A dermoscopic image of a skin lesion.
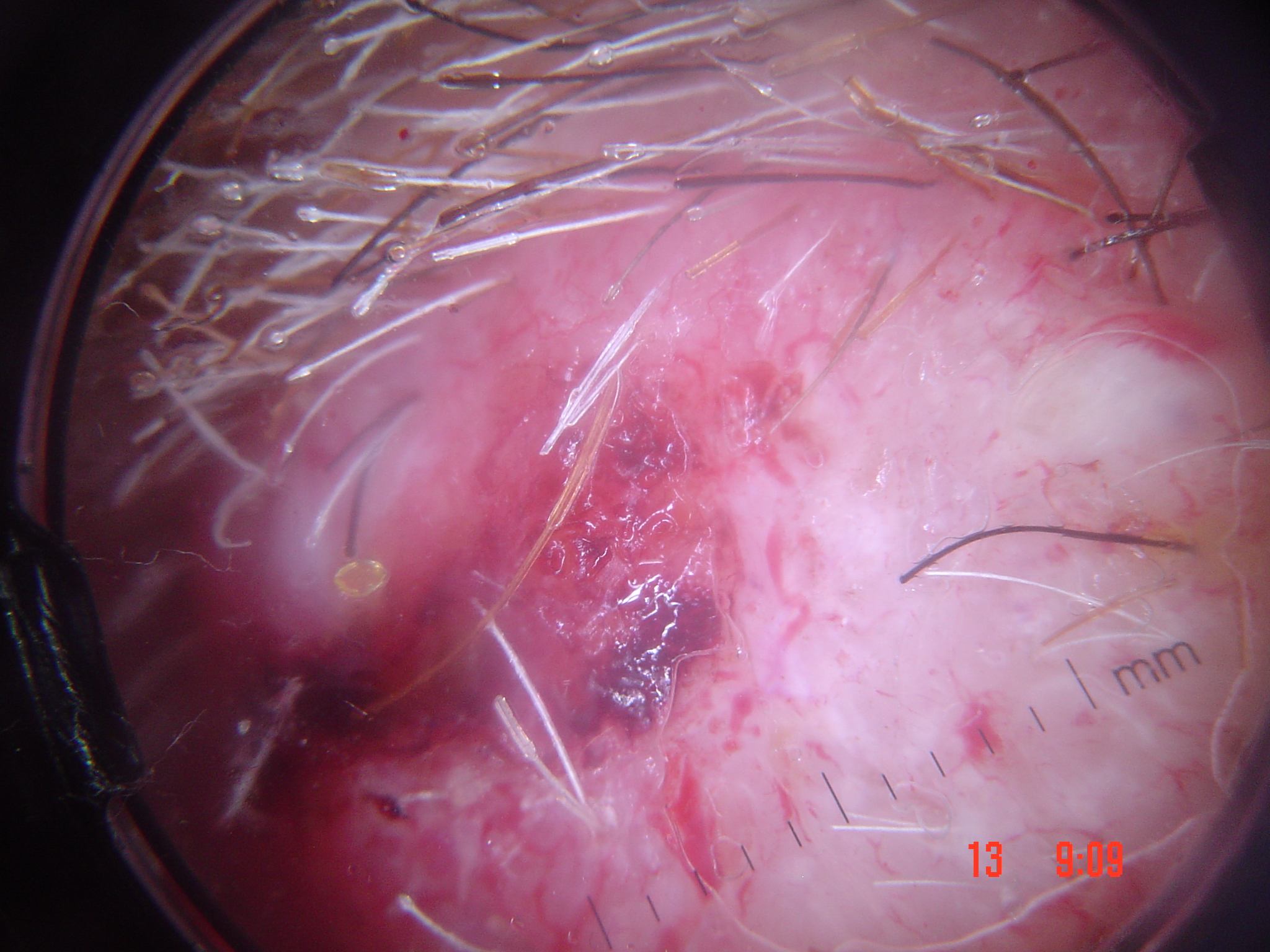Case:
The morphology is that of a keratinocytic lesion.
Pathology:
Biopsy-confirmed as a malignancy — a squamous cell carcinoma.